Texture is reported as raised or bumpy and fluid-filled; this image was taken at an angle; reported lesion symptoms include bothersome appearance; the affected area is the arm — 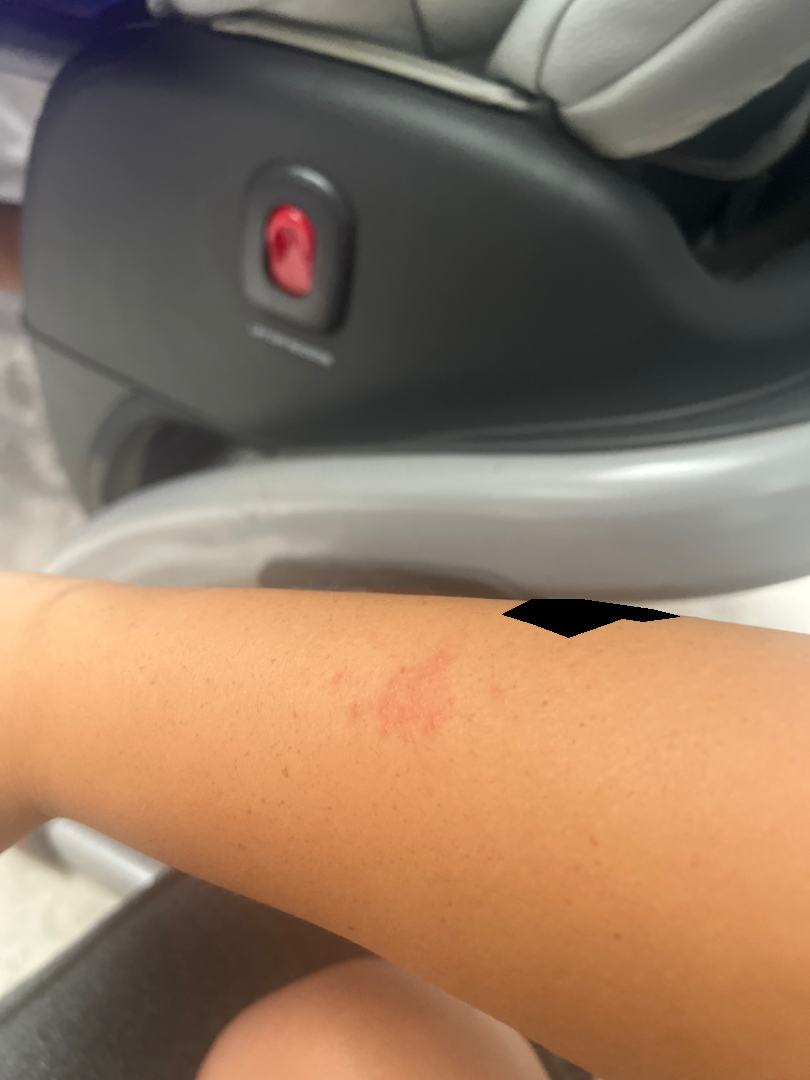Assessment: The reviewing dermatologist was unable to assign a differential diagnosis from the image.